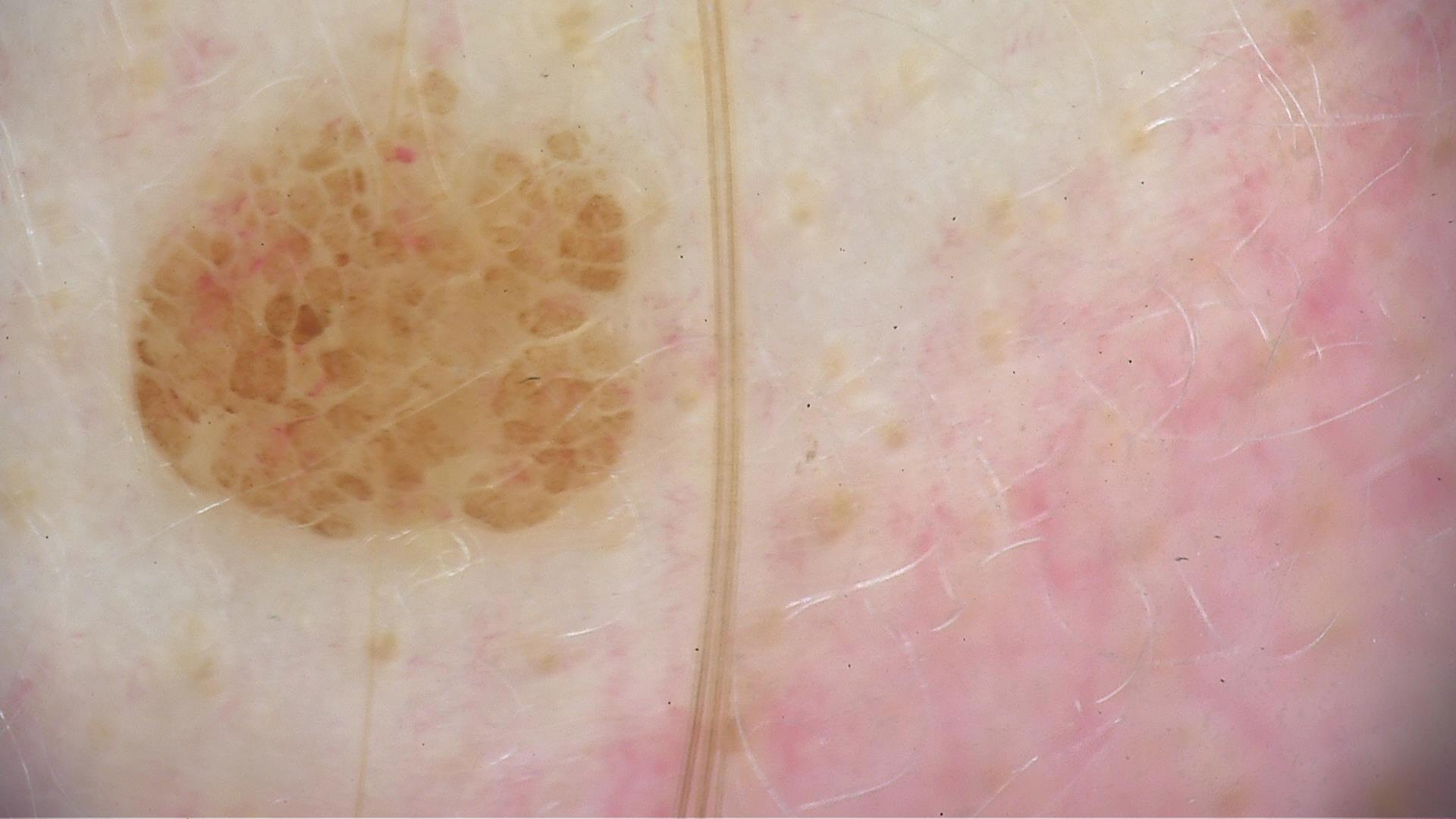A dermoscopic image of a skin lesion.
The diagnostic label was a banal lesion — a compound nevus.